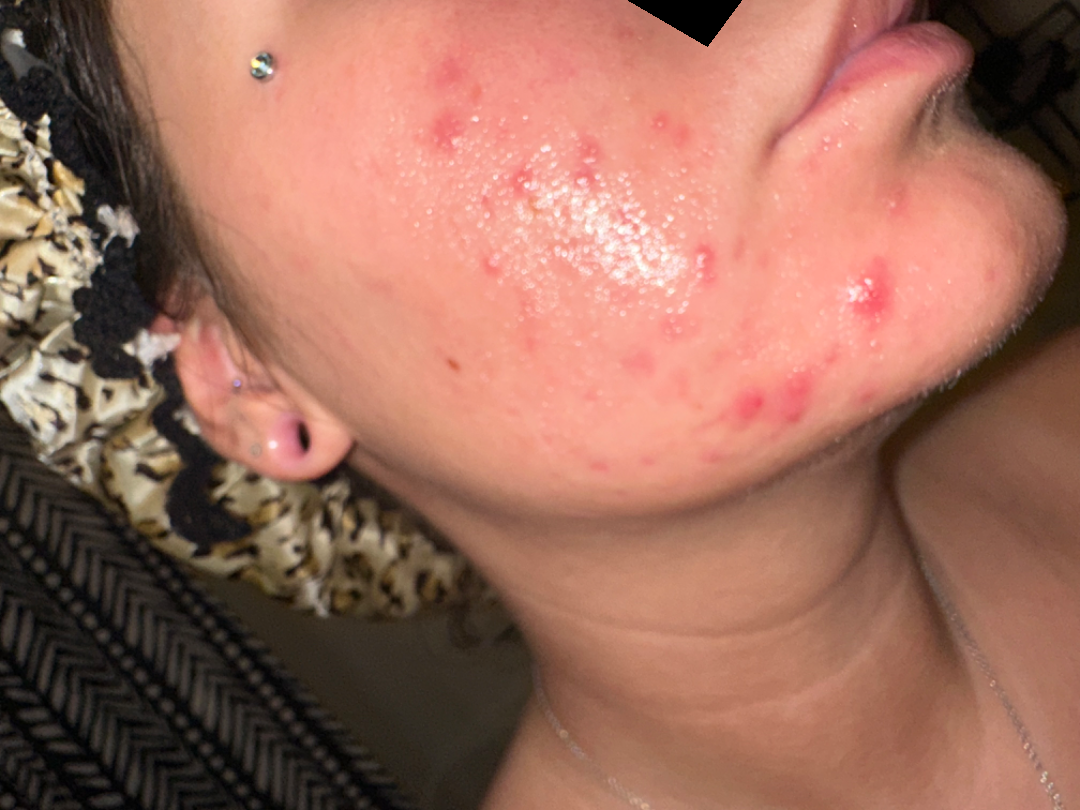The leading consideration is Acne; an alternative is Rosacea; the differential also includes Perioral Dermatitis.